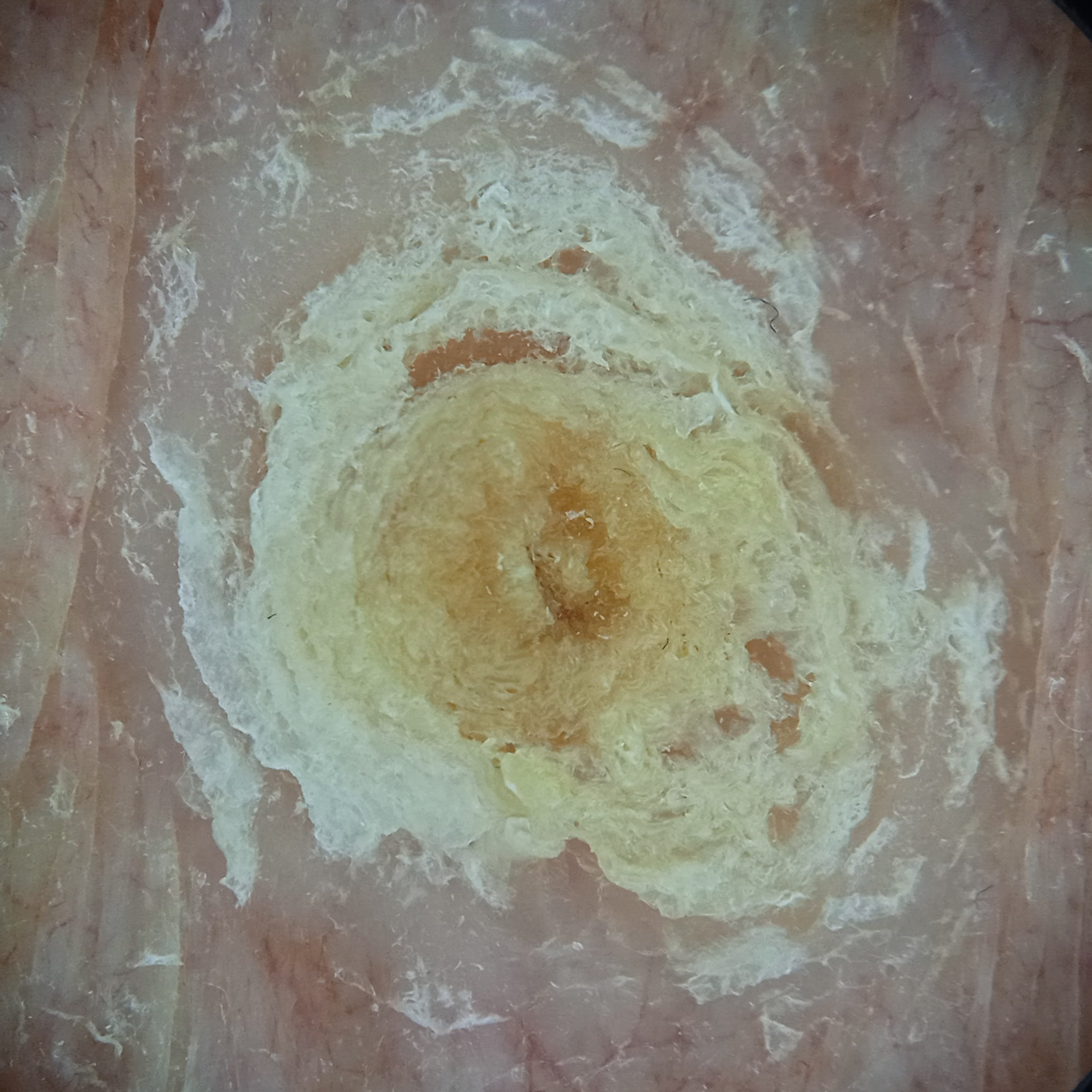{"referral": "research study (no referral diagnosis)", "image": "dermoscopy", "patient": {"age": 92, "sex": "female"}, "sun_reaction": "skin tans without first burning", "lesion_location": "the torso", "lesion_size": {"diameter_mm": 12.5}, "diagnosis": {"name": "squamous cell carcinoma", "malignancy": "malignant"}}